This is a close-up image · skin tone: non-clinician graders estimated Monk skin tone scale 2 (US pool) or 3 (India pool): 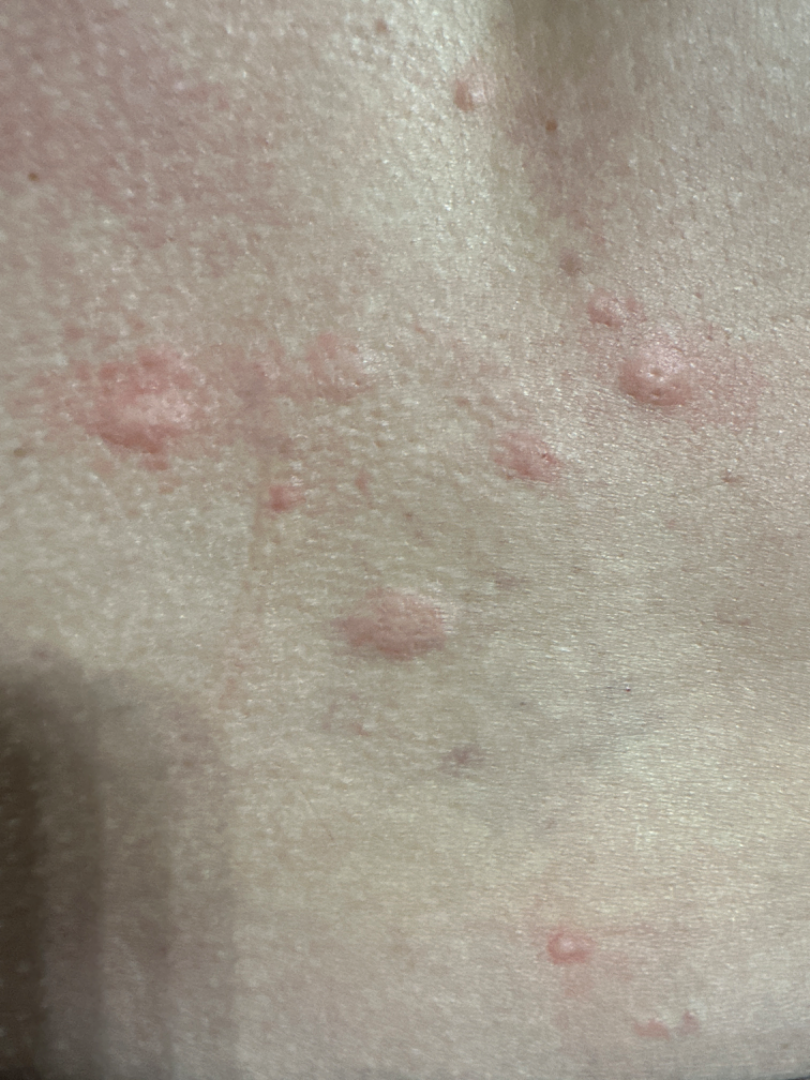No differential diagnosis could be assigned on photographic review.